Dermoscopy of a skin lesion.
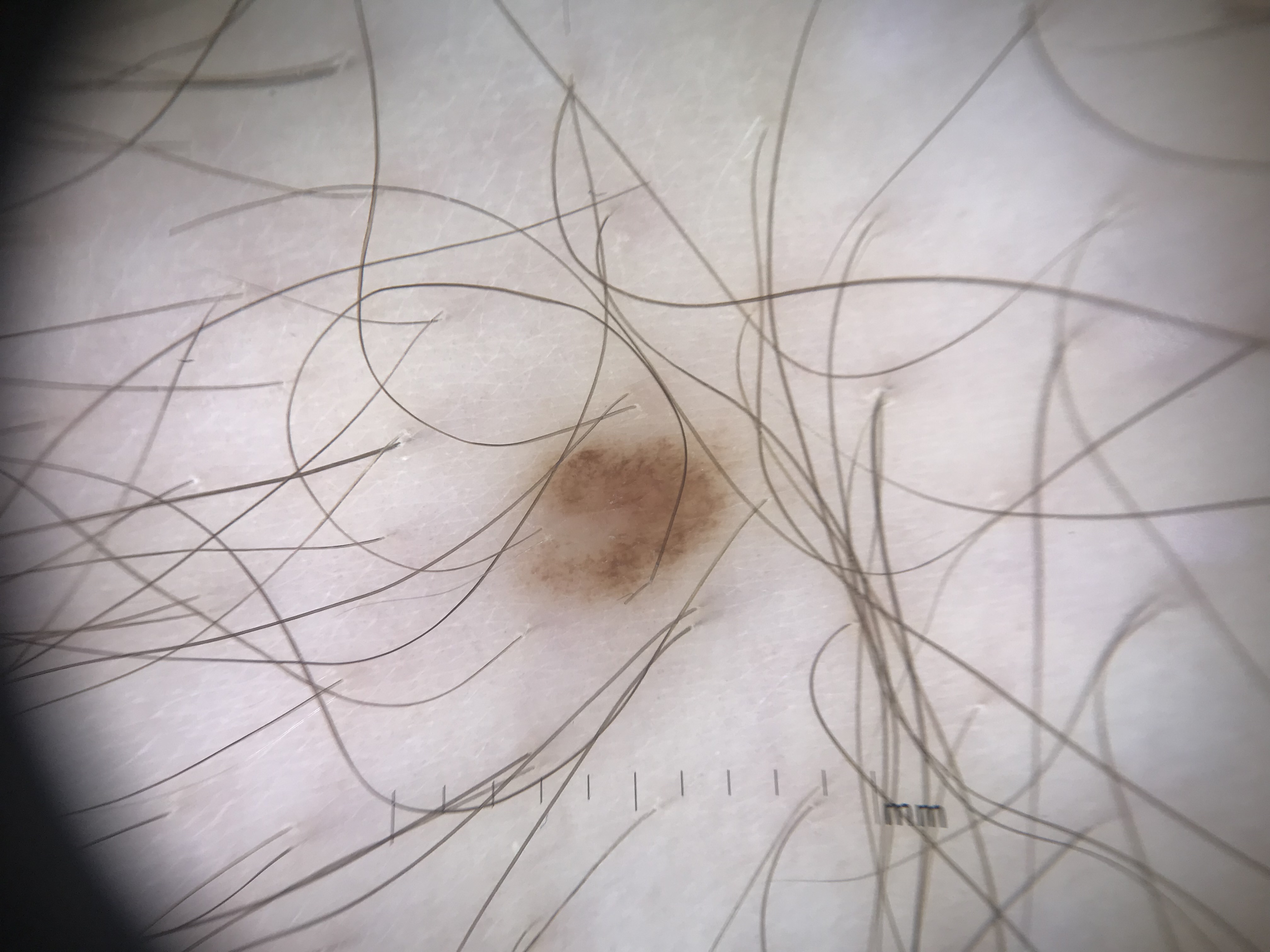{"diagnosis": {"name": "dysplastic junctional nevus", "code": "jd", "malignancy": "benign", "super_class": "melanocytic", "confirmation": "expert consensus"}}